A dermoscopic view of a skin lesion.
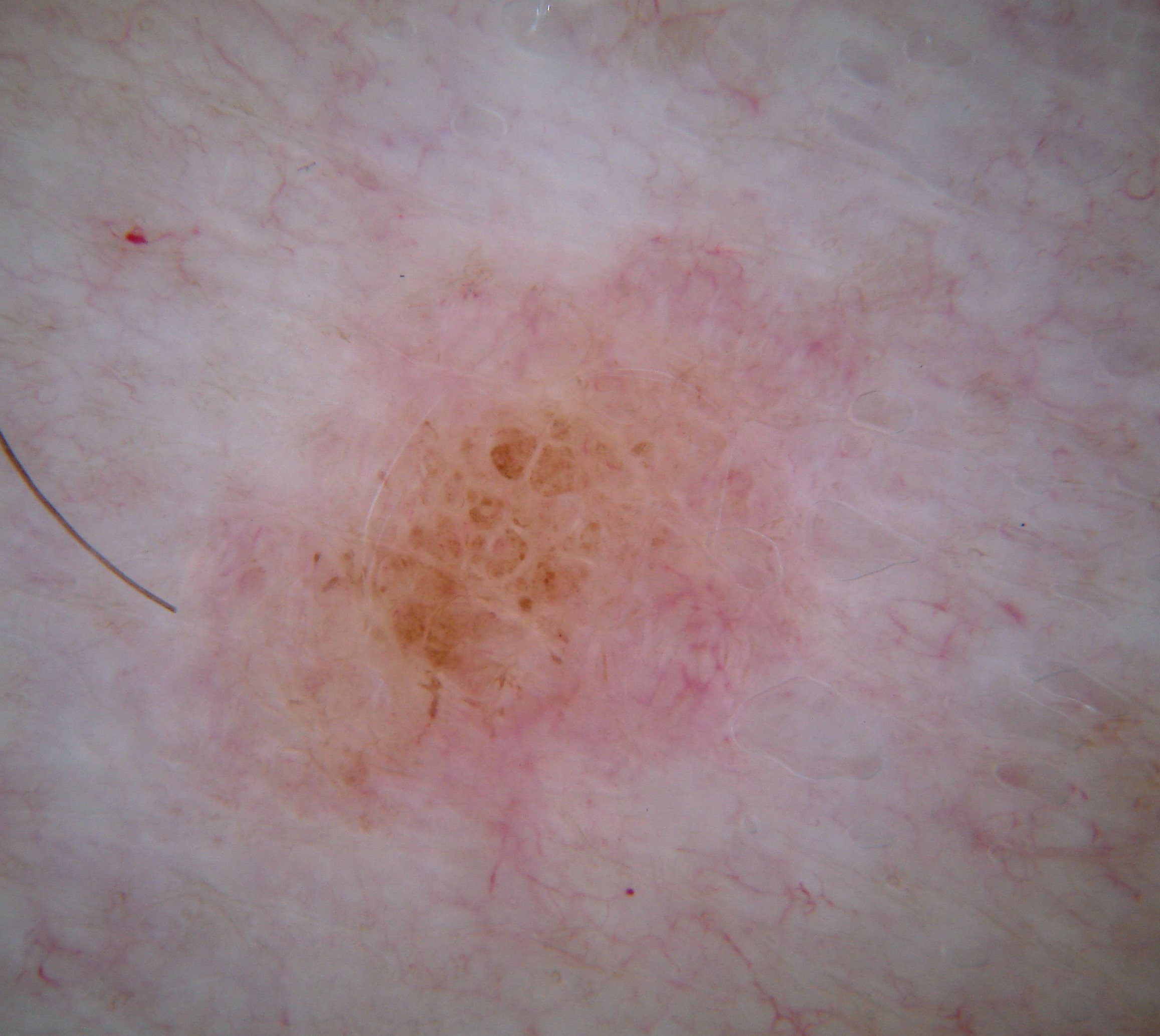The lesion spans x1=159 y1=238 x2=875 y2=943. The dermoscopic pattern shows globules; no streaks, negative network, milia-like cysts, or pigment network. Consistent with a melanocytic nevus.